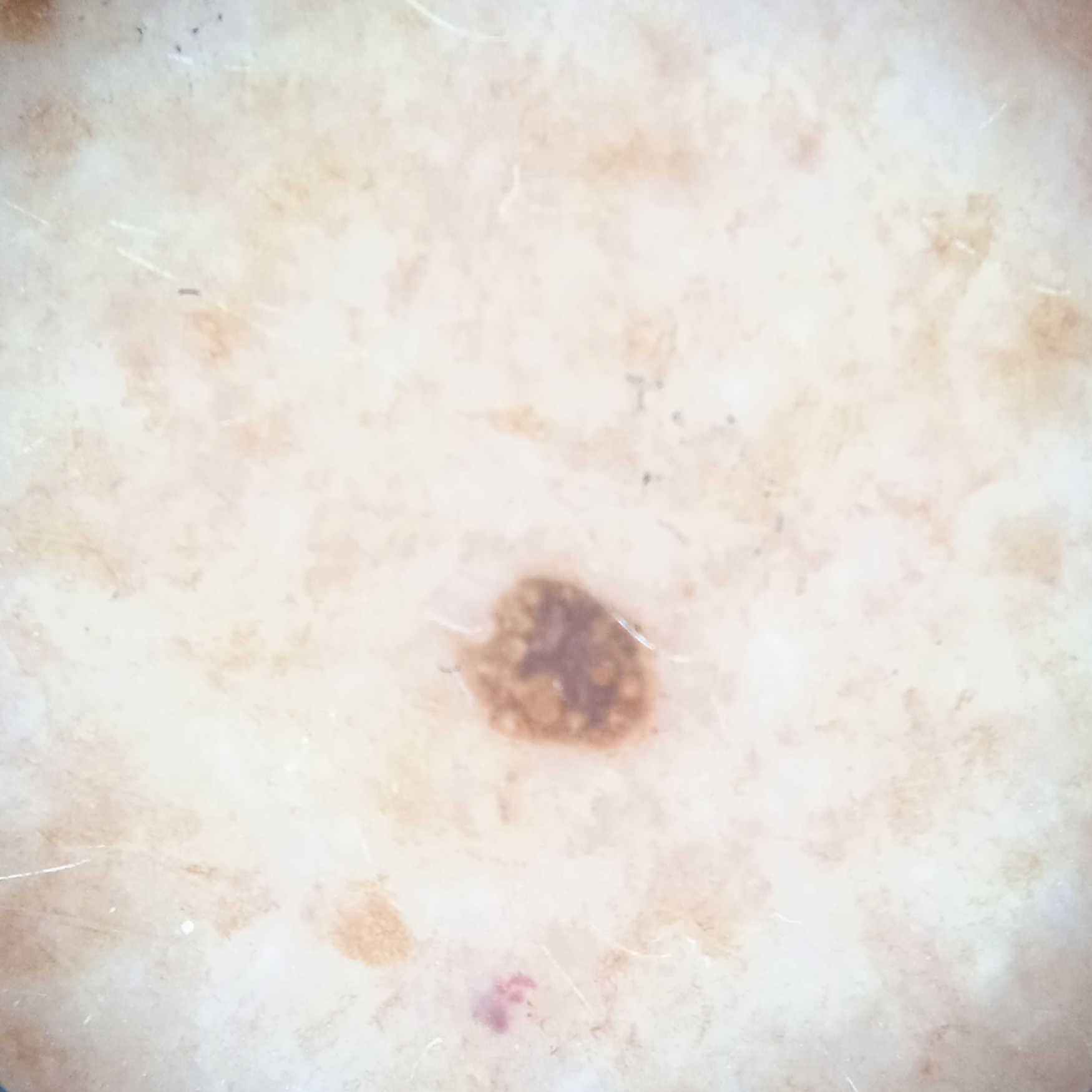Q: How does the patient's skin react to sun?
A: skin tans without first burning
Q: What is the patient's nevus burden?
A: numerous melanocytic nevi
Q: Why was this imaged?
A: research study (no referral diagnosis)
Q: Patient demographics?
A: female, 78 years old
Q: What is the imaging modality?
A: dermoscopy
Q: What is the anatomic site?
A: an arm
Q: Lesion size?
A: 2.4 mm
Q: What was the diagnosis?
A: seborrheic keratosis (dermatologist consensus)